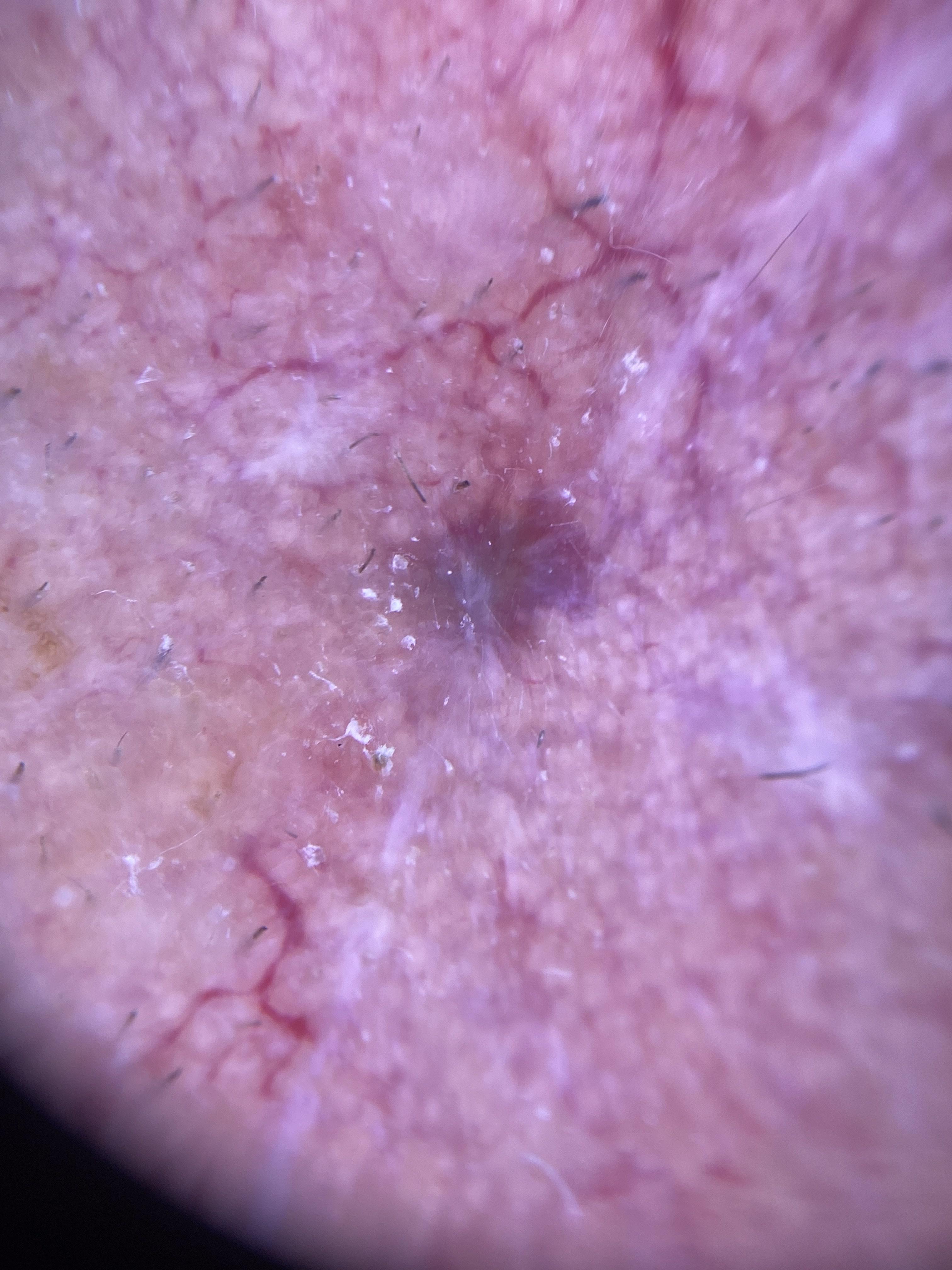Q: What kind of image is this?
A: contact-polarized dermoscopy
Q: What does the history note?
A: a previous melanoma
Q: What is the patient's skin type?
A: II
Q: Patient demographics?
A: male, aged 83 or over
Q: What is the anatomic site?
A: the head or neck
Q: What is this lesion?
A: Squamous cell carcinoma (biopsy-proven)